A dermoscopic image of a skin lesion.
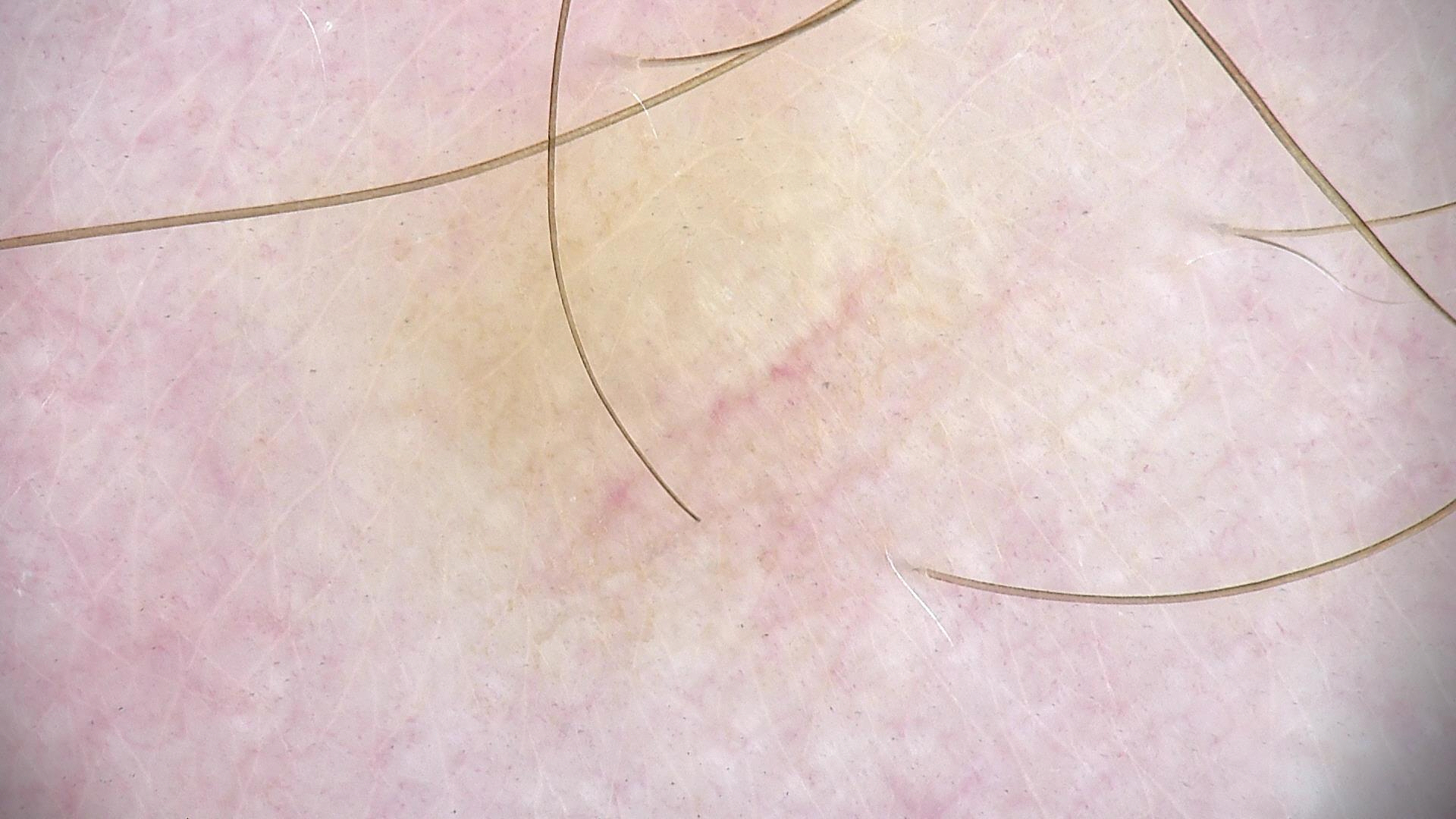Labeled as a benign lesion — a dysplastic junctional nevus.